The patient is female · the patient reported no systemic symptoms · skin tone: Fitzpatrick II; human graders estimated a MST of 2 · the contributor reports itching · located on the back of the torso · this is a close-up image · the condition has been present for about one day · the lesion is described as raised or bumpy: 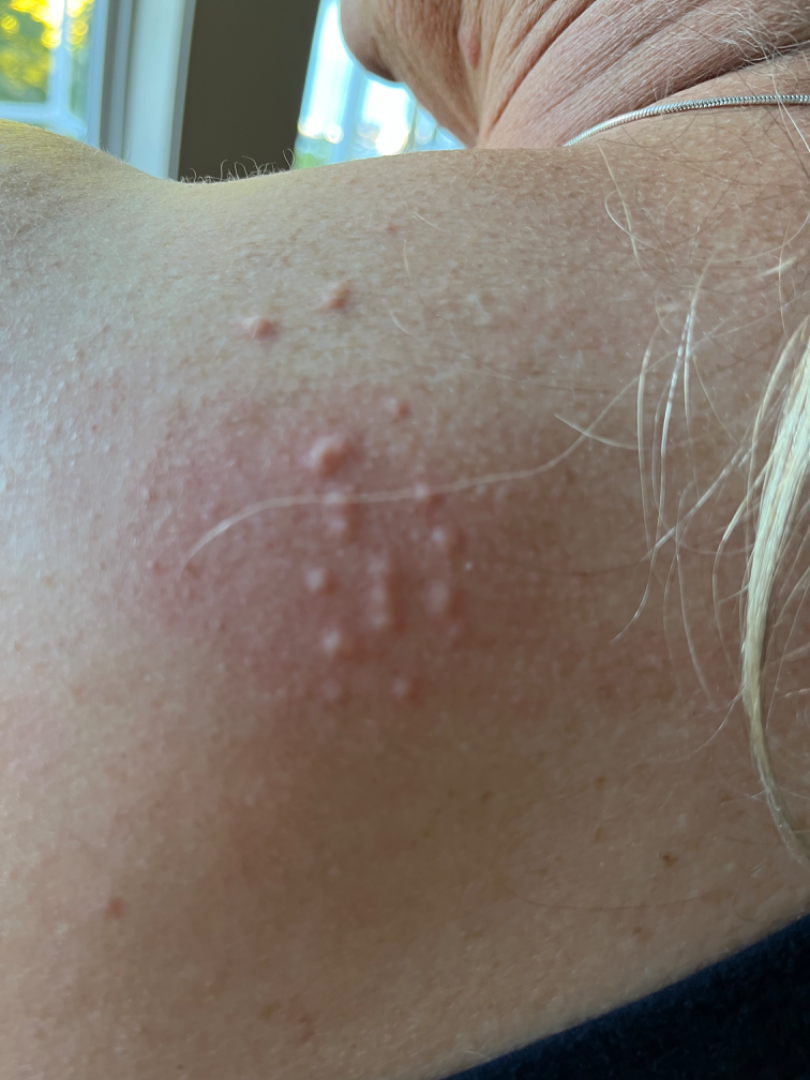assessment: ungradable on photographic review.